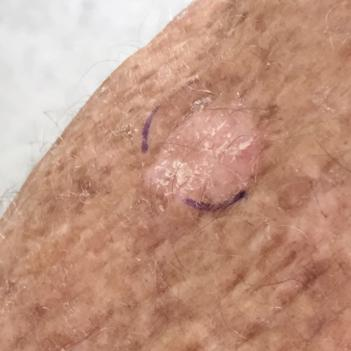Case:
* image type: smartphone clinical photo
* Fitzpatrick: II
* subject: female, in their 70s
* site: a forearm
* diameter: 4x4 mm
* symptoms: itching, growth
* diagnostic label: actinic keratosis (clinical consensus)